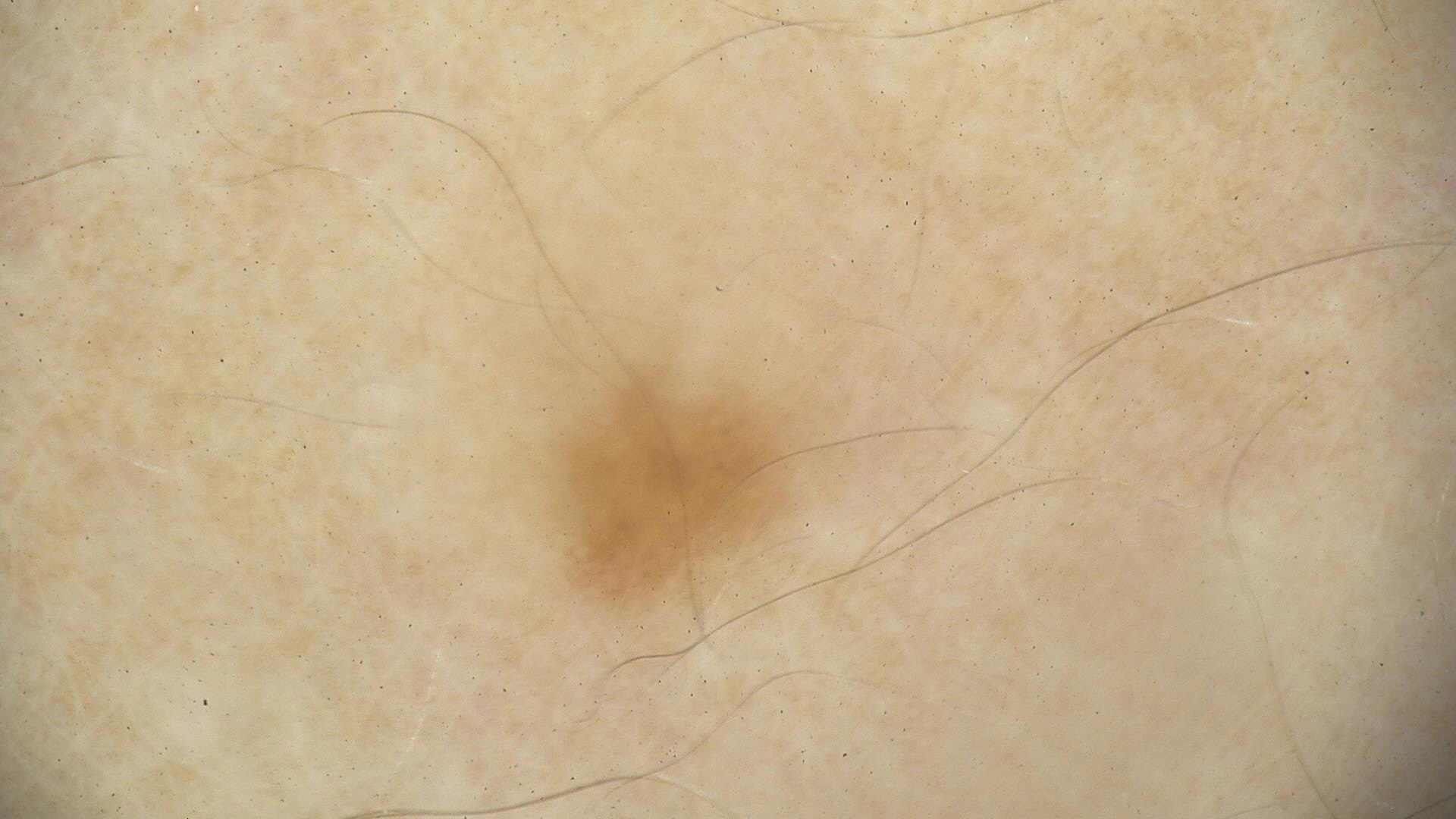A dermoscopic image of a skin lesion. Diagnosed as a lentigo simplex.